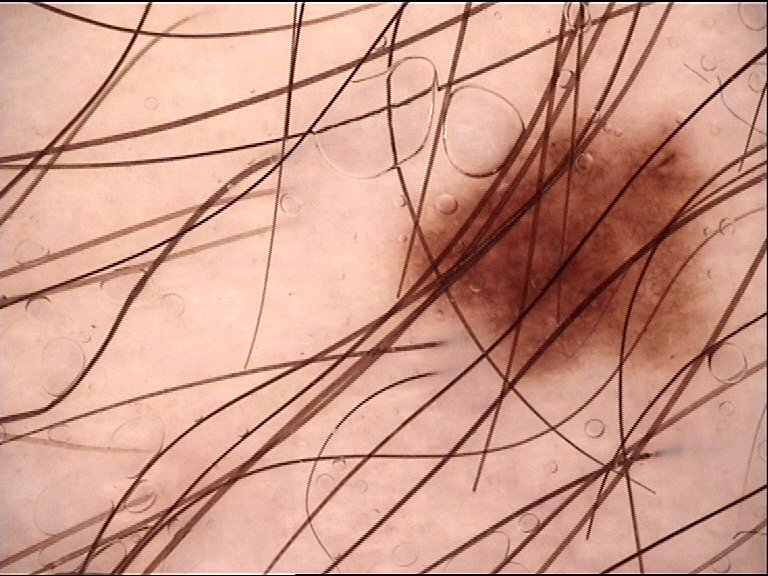The diagnostic label was a dysplastic junctional nevus.